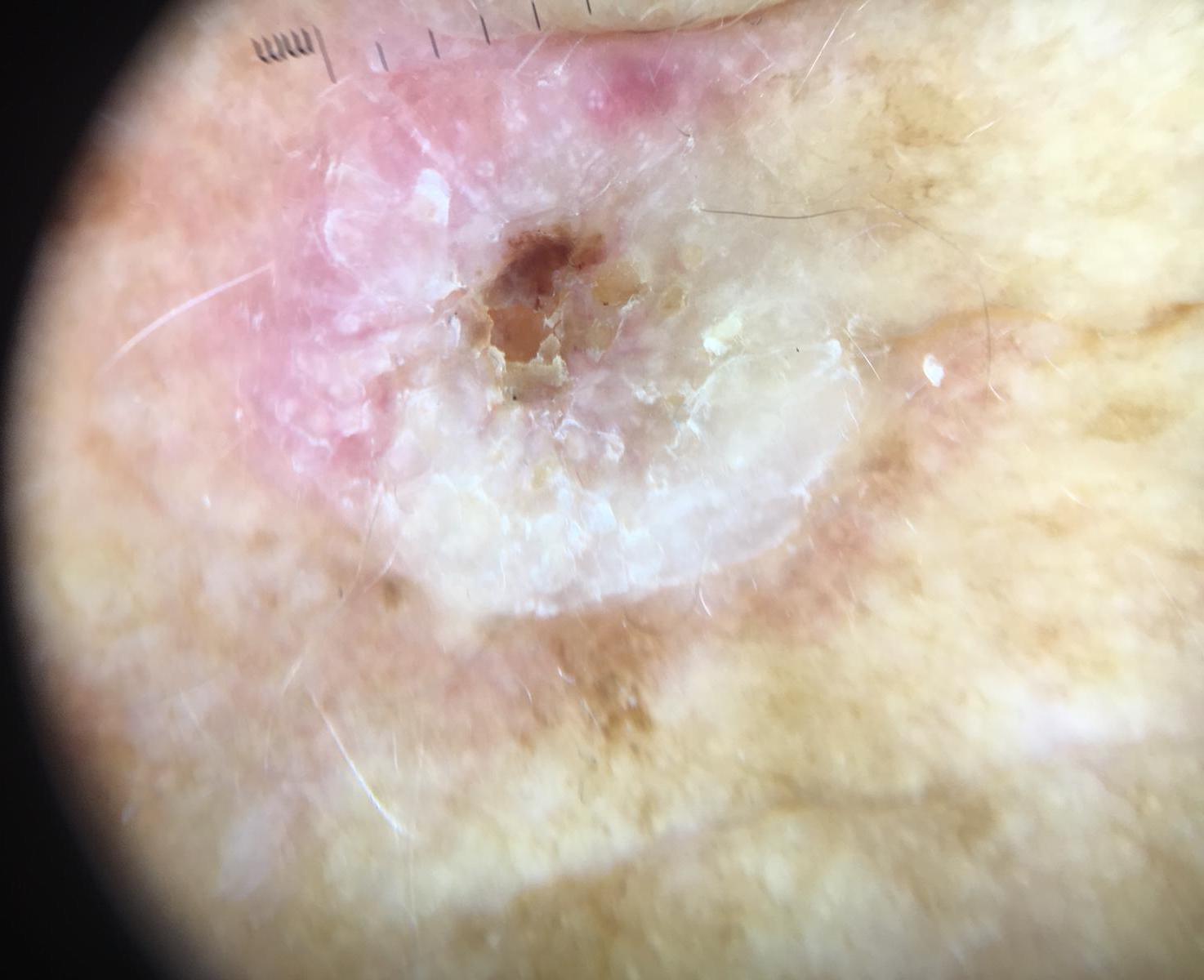<dermoscopy>
  <image>dermatoscopy</image>
  <diagnosis>
    <name>squamous cell carcinoma</name>
    <code>scc</code>
    <malignancy>malignant</malignancy>
    <super_class>non-melanocytic</super_class>
    <confirmation>histopathology</confirmation>
  </diagnosis>
</dermoscopy>